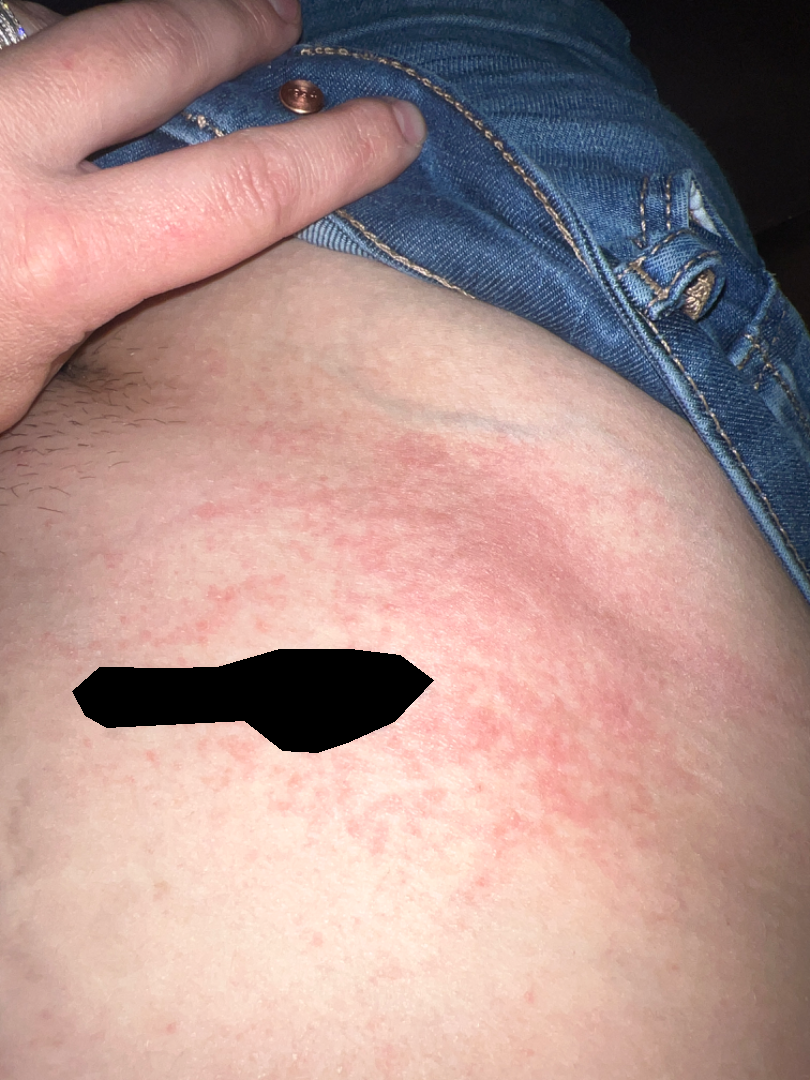Review: The reviewer was unable to grade this case for skin condition. Patient information: Female patient, age 30–39. Reported duration is about one day. Self-categorized by the patient as a rash. The lesion involves the leg. The patient indicates burning and itching. The photograph is a close-up of the affected area. Texture is reported as raised or bumpy.